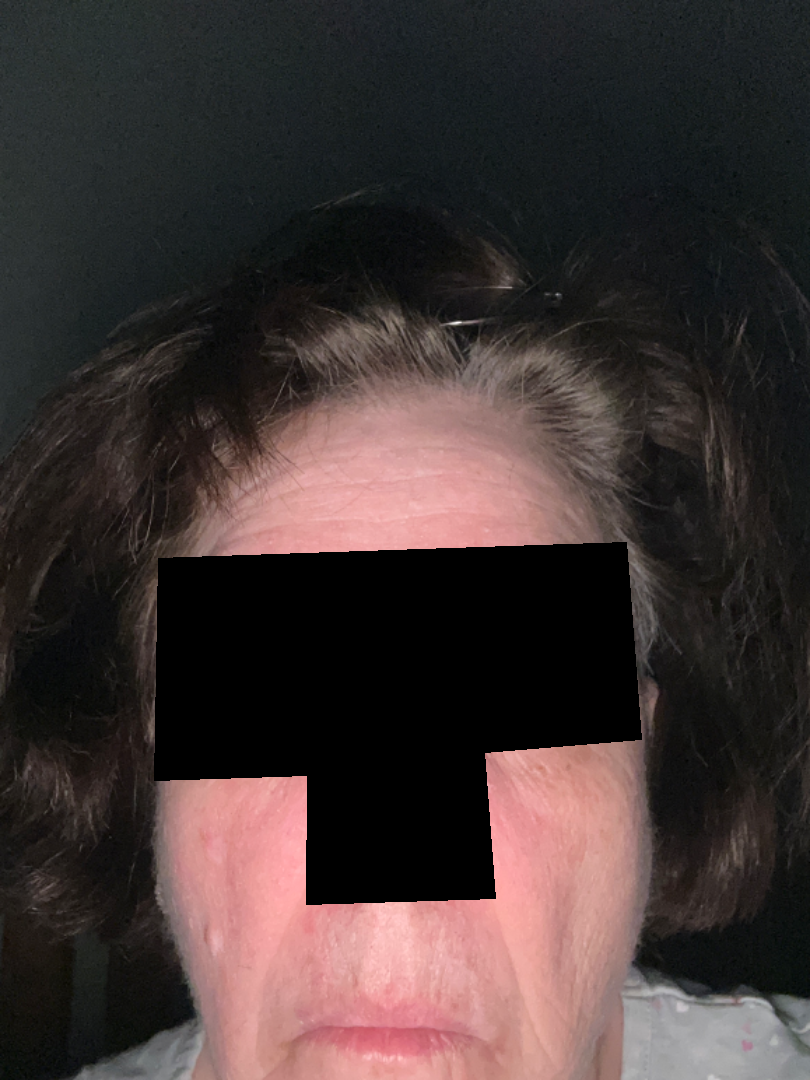This image was taken at a distance. In keeping with Seborrheic Dermatitis.